A female subject 72 years old; acquired for a research image collection, with no referral diagnosis; a macroscopic clinical photograph of a skin lesion: 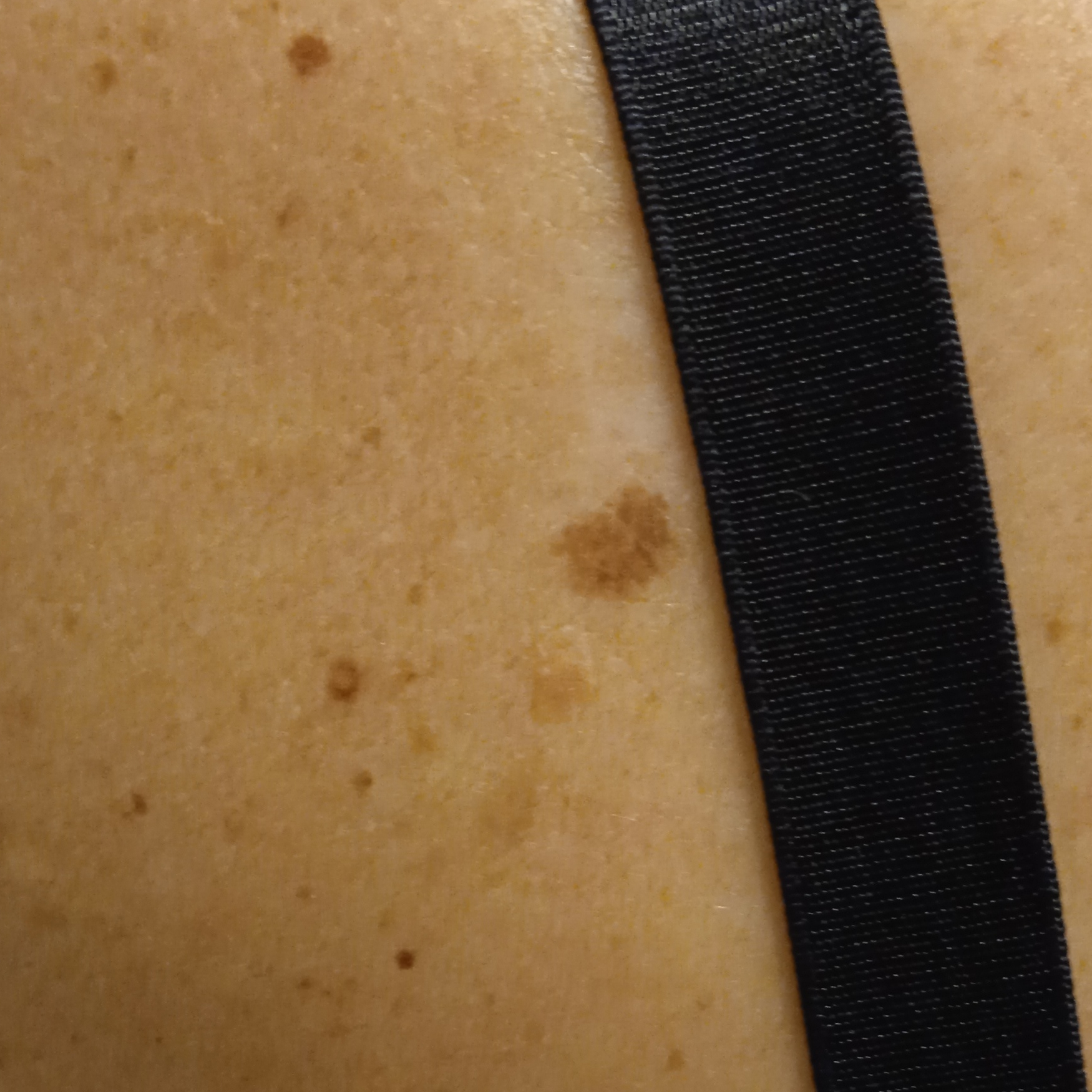{
  "lesion_location": "the back",
  "lesion_size": {
    "diameter_mm": 7.1
  },
  "diagnosis": {
    "name": "seborrheic keratosis",
    "malignancy": "benign"
  }
}